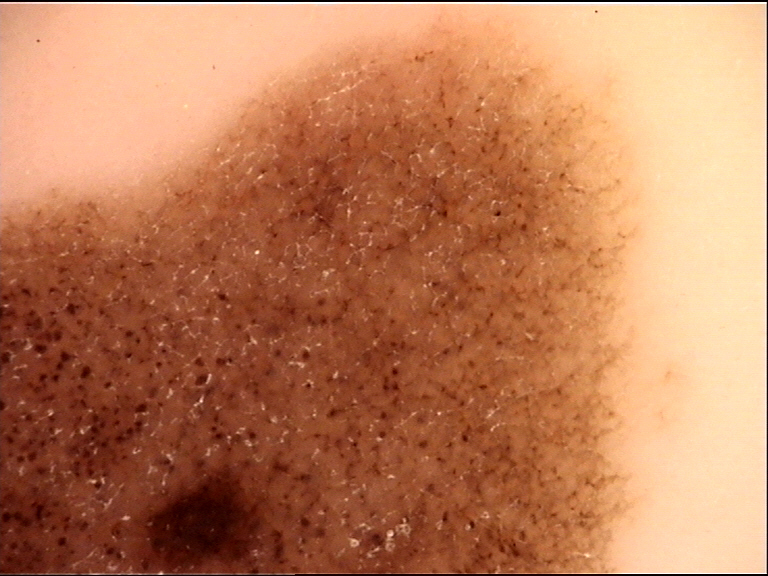Labeled as a congenital compound nevus.